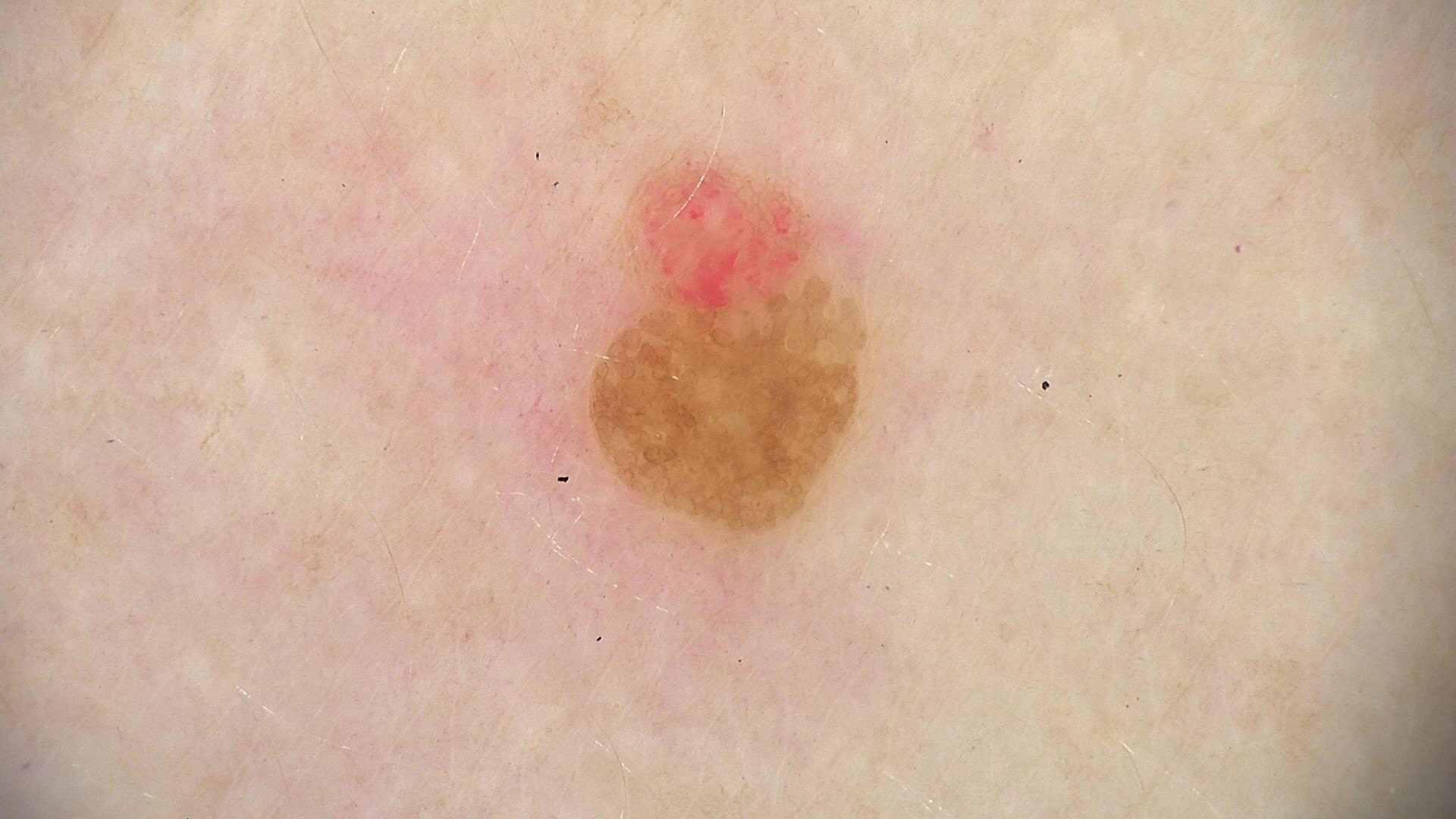Findings: A skin lesion imaged with a dermatoscope. The morphology is that of a keratinocytic lesion. Impression: The diagnosis was a benign lesion — a seborrheic keratosis.